A subject age 40 · a clinical photograph of a skin lesion: 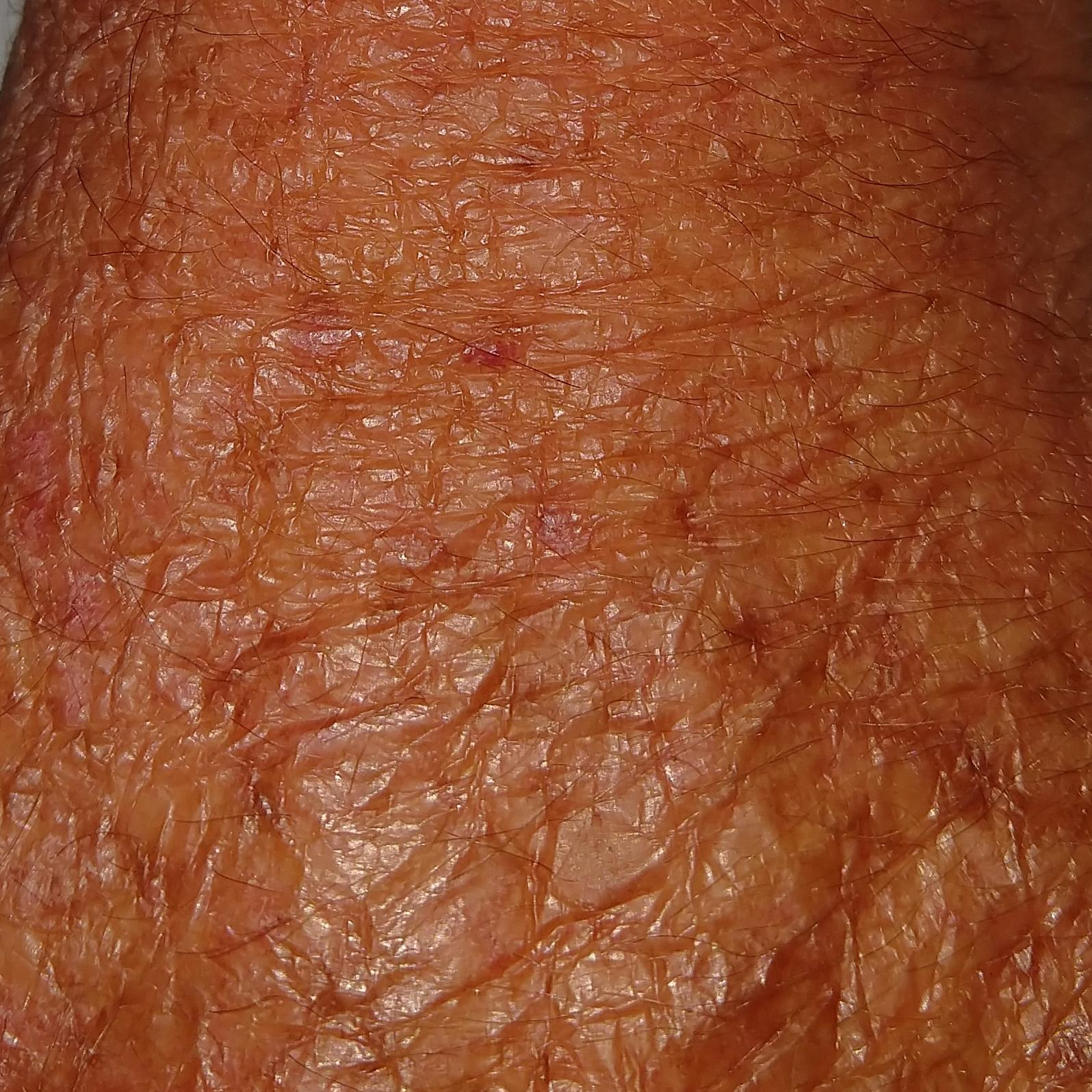Clinical context:
Located on a hand. Asymptomatic by report.
Conclusion:
Consistent with a premalignant lesion — an actinic keratosis.